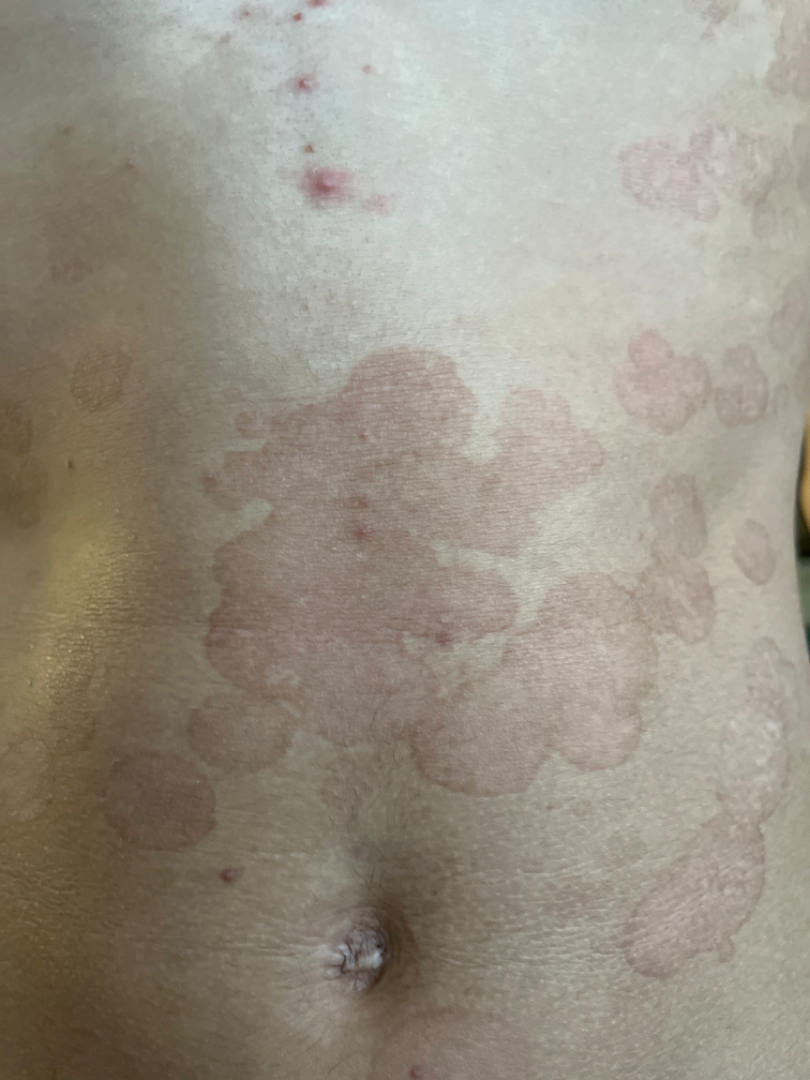{
  "differential": "Psoriasis"
}